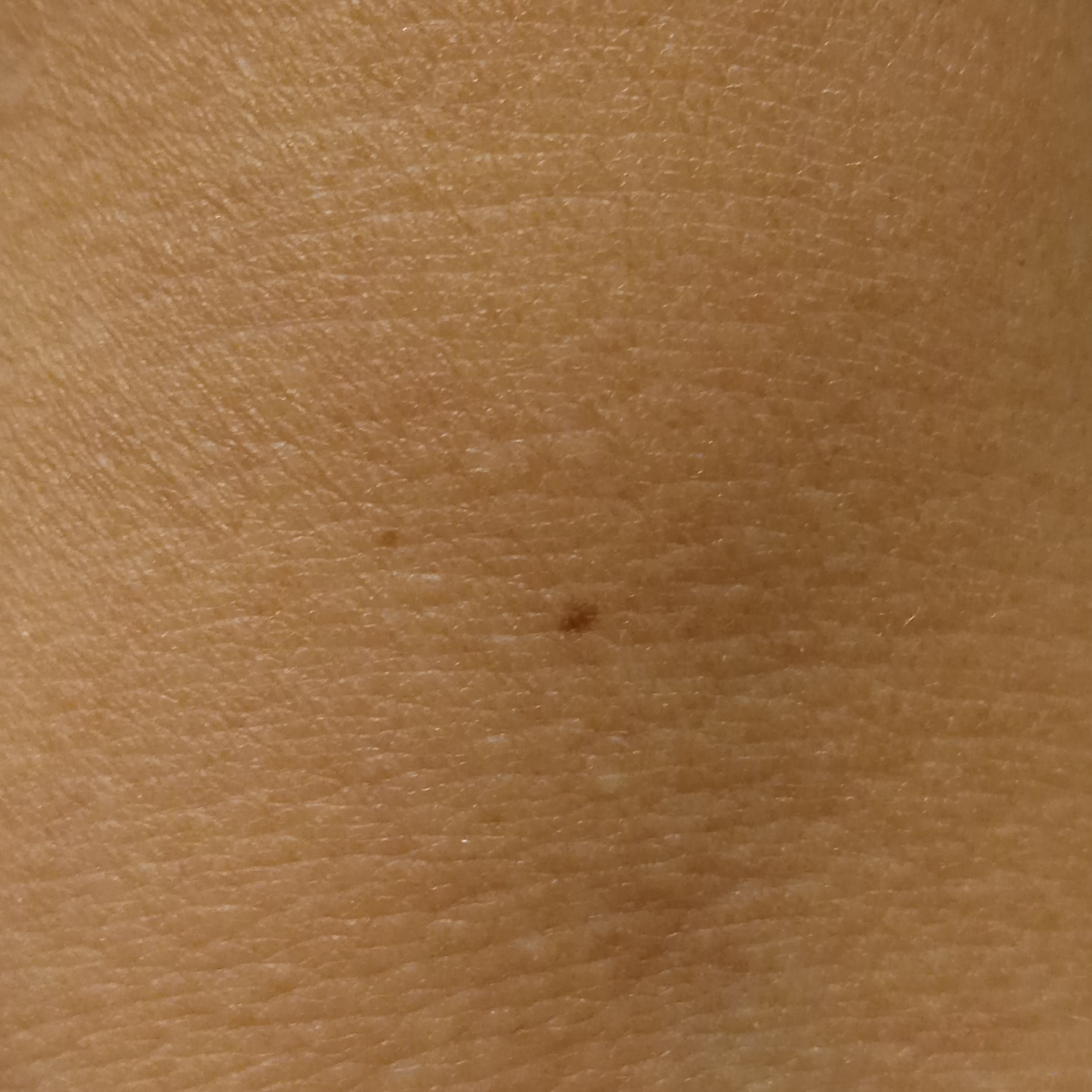Summary: The patient describes having a moderate number of moles. The patient says their skin tans without first burning. A female patient age 58. On a questionnaire the patient reported a personal history of skin cancer, a family history of skin cancer, a personal history of cancer, and no sunbed use. Imaged for a research study, with no referral diagnosis recorded. The lesion involves an arm. The lesion is about 1.9 mm across. Impression: The dermatologists' assessment was a melanocytic nevus.